The patient described the issue as a rash · the subject is 30–39, female · the lesion involves the arm · the contributor reports the lesion is raised or bumpy · Fitzpatrick skin type III; human graders estimated Monk Skin Tone 2 or 4 (two reviewer pools disagreed) · the photograph was taken at a distance — 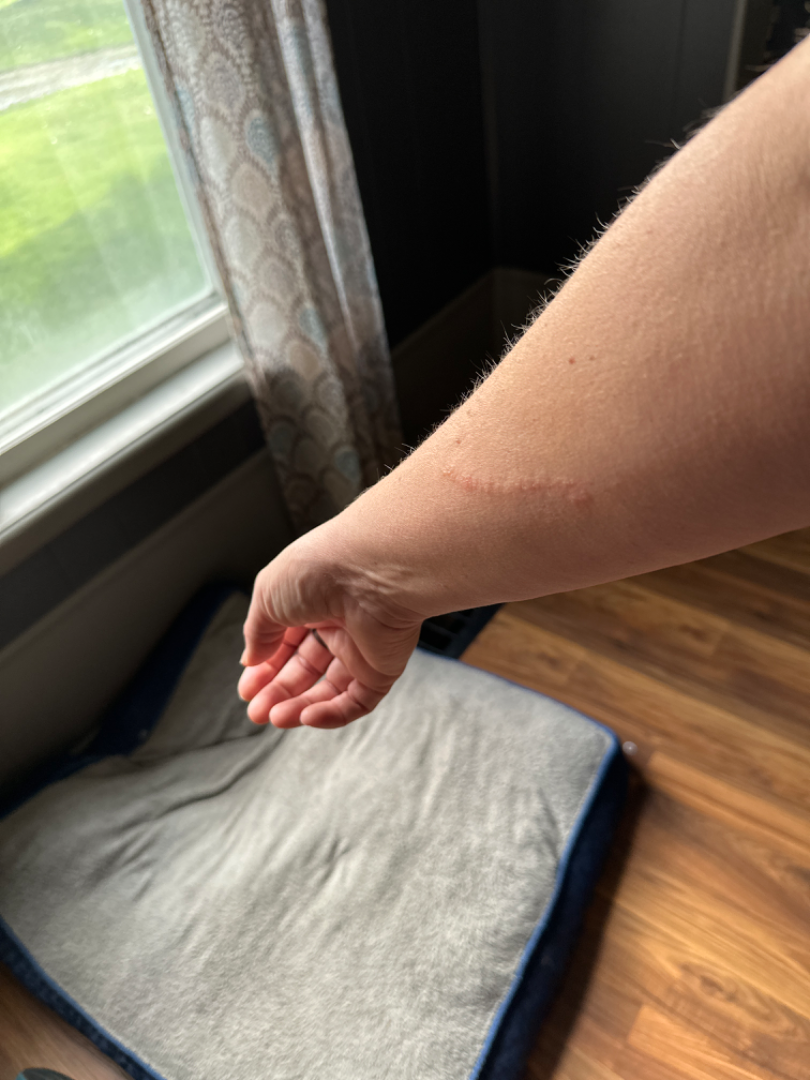The image was not sufficient for the reviewer to characterize the skin condition.